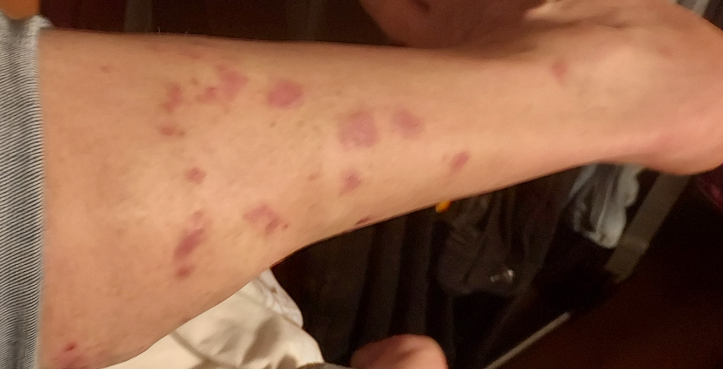Patient information: The patient reports associated fatigue. Present for three to twelve months. The patient is 50–59, male. The patient reports enlargement, itching and bothersome appearance. FST III. Located on the leg and top or side of the foot. An image taken at an angle. Review: The reviewing panel's impression was: Lichen planus/lichenoid eruption and Nodular vasculitis were considered with similar weight; a remote consideration is Psoriasis; less likely is Eczema; less probable is Pseudolymphoma.